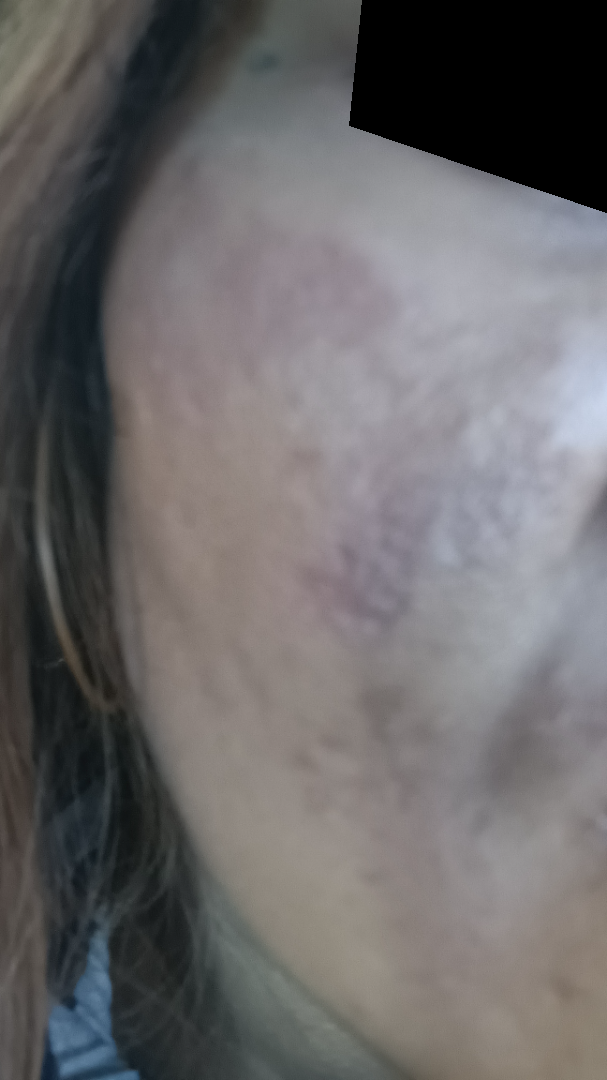Clinical context:
Skin tone: Fitzpatrick IV. The patient considered this acne. The lesion is described as fluid-filled, rough or flaky and raised or bumpy. An image taken at a distance. The contributor notes the condition has been present for more than five years. The contributor is female. Located on the head or neck.
Assessment:
On photographic review: Melasma (weight 0.33); Scar Condition (weight 0.33); Post-Inflammatory hyperpigmentation (weight 0.33).